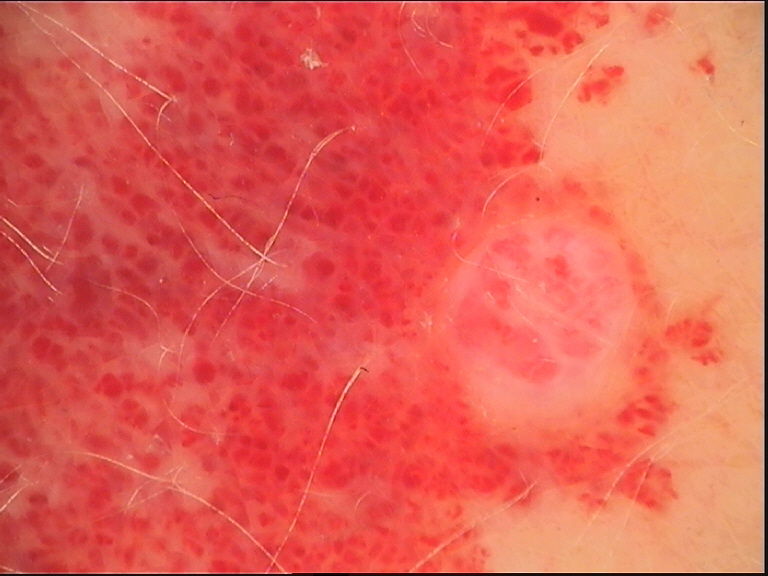The morphology is that of a vascular lesion. Classified as a hemangioma.